Close-up view, the head or neck is involved: 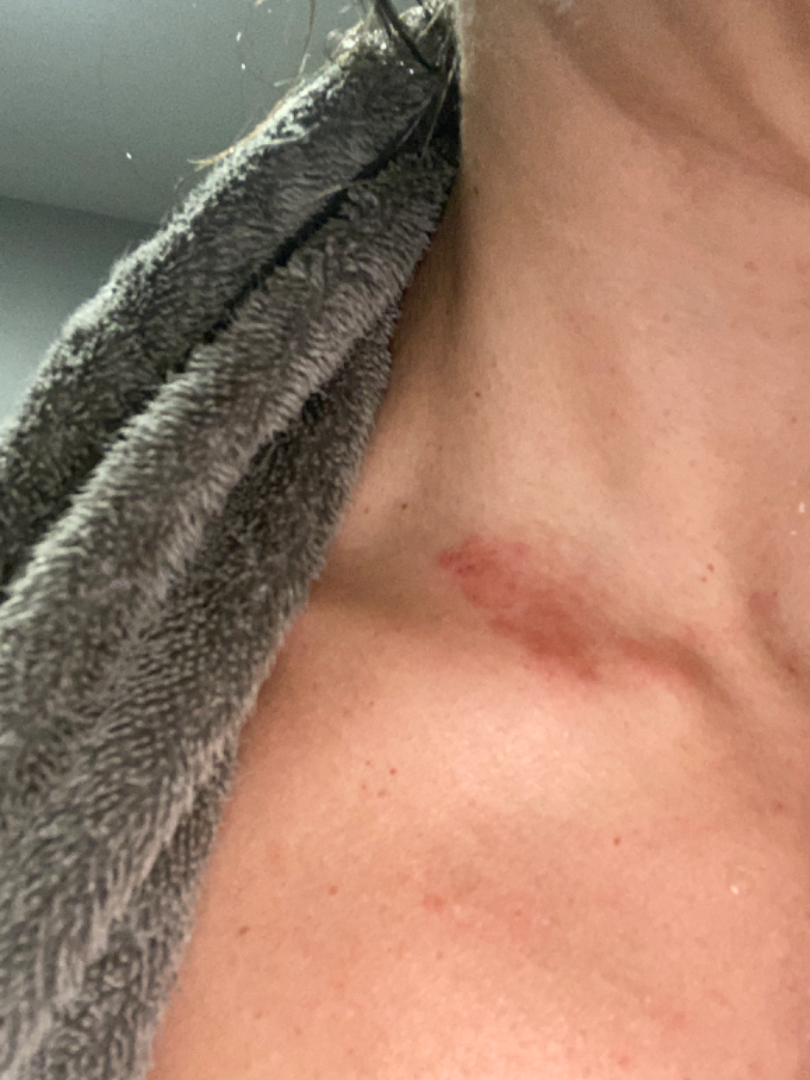assessment: not assessable
symptoms:
  - enlargement
  - itching
  - bothersome appearance
duration: less than one week
patient_category: a rash